The photo was captured at an angle, located on the arm.
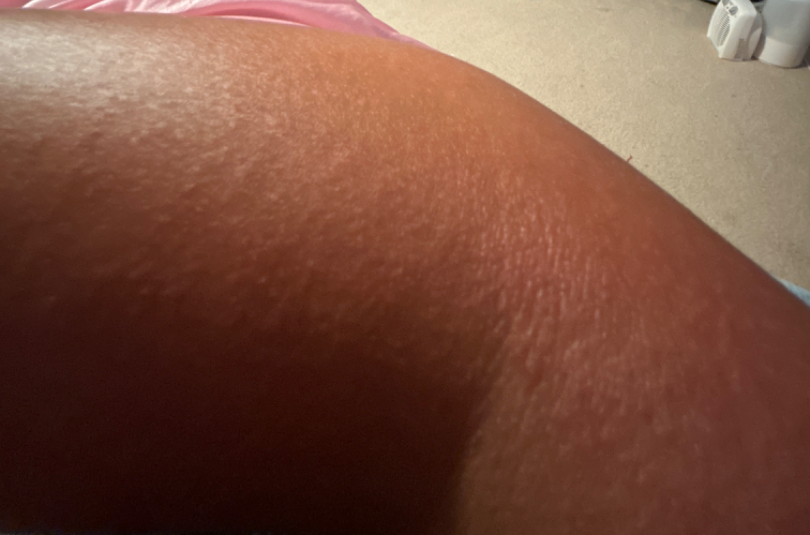• assessment — indeterminate from the photograph
• lesion texture — raised or bumpy
• systemic symptoms — none reported
• symptoms — bothersome appearance, itching, enlargement and burning
• symptom duration — less than one week
• patient describes the issue as — a rash